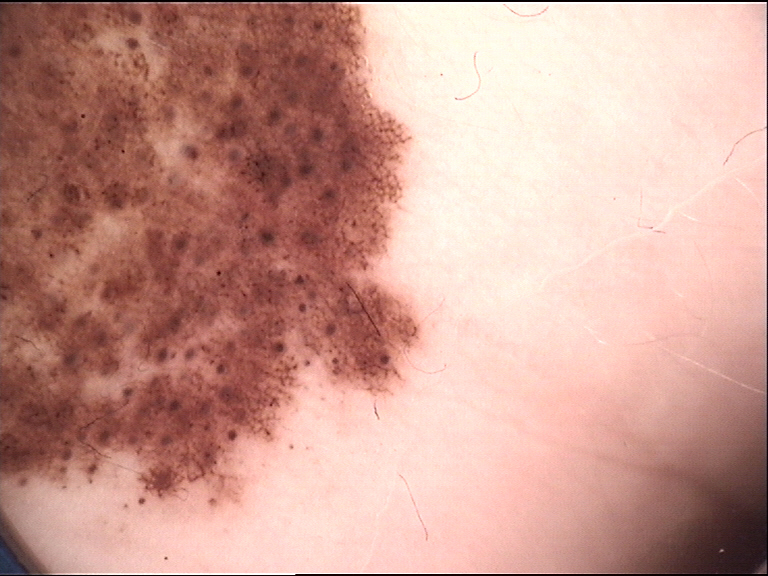A dermoscopy image of a single skin lesion. The architecture is that of a banal lesion. The diagnosis was a congenital compound nevus.